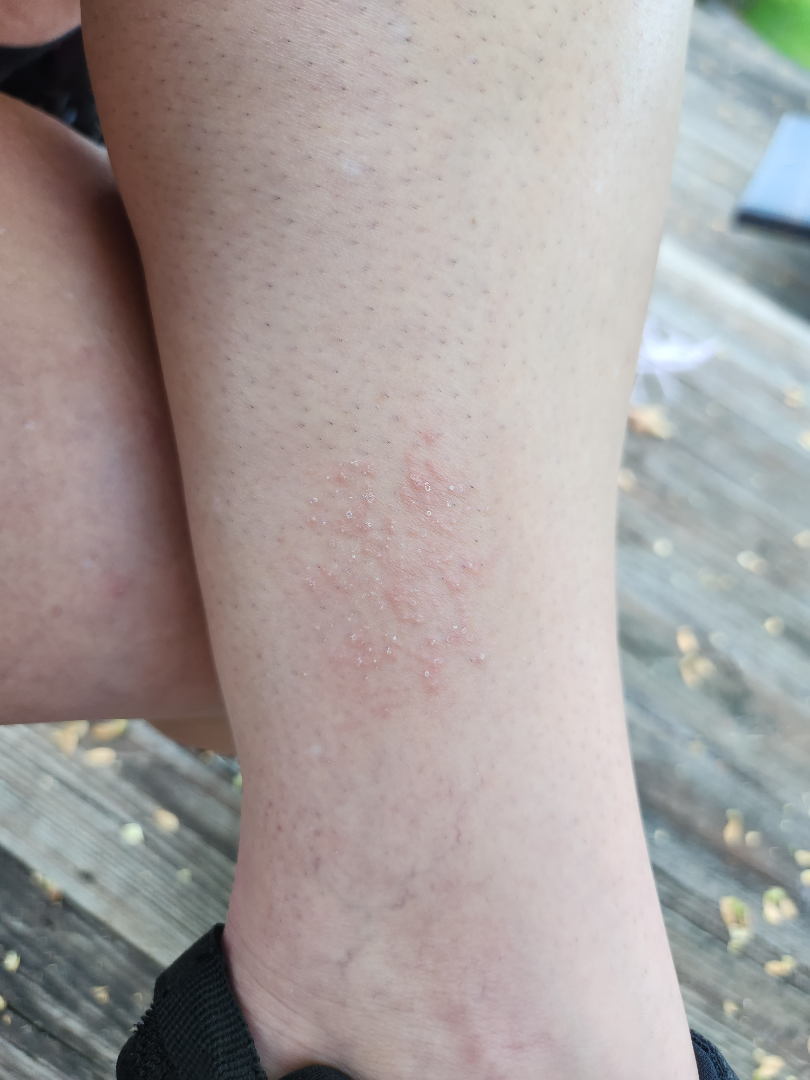The patient indicates the condition has been present for one to four weeks.
An image taken at a distance.
The contributor is a female aged 30–39.
The patient indicates the lesion is raised or bumpy.
The leg is involved.
Reported lesion symptoms include itching.
Self-categorized by the patient as a rash.
The reviewing clinician's impression was: the differential is split between Keratosis pilaris and Lichen spinulosus; less probable is Folliculitis.